The referring clinician suspected melanoma. Dermoscopy of a skin lesion. A female subject age 50: 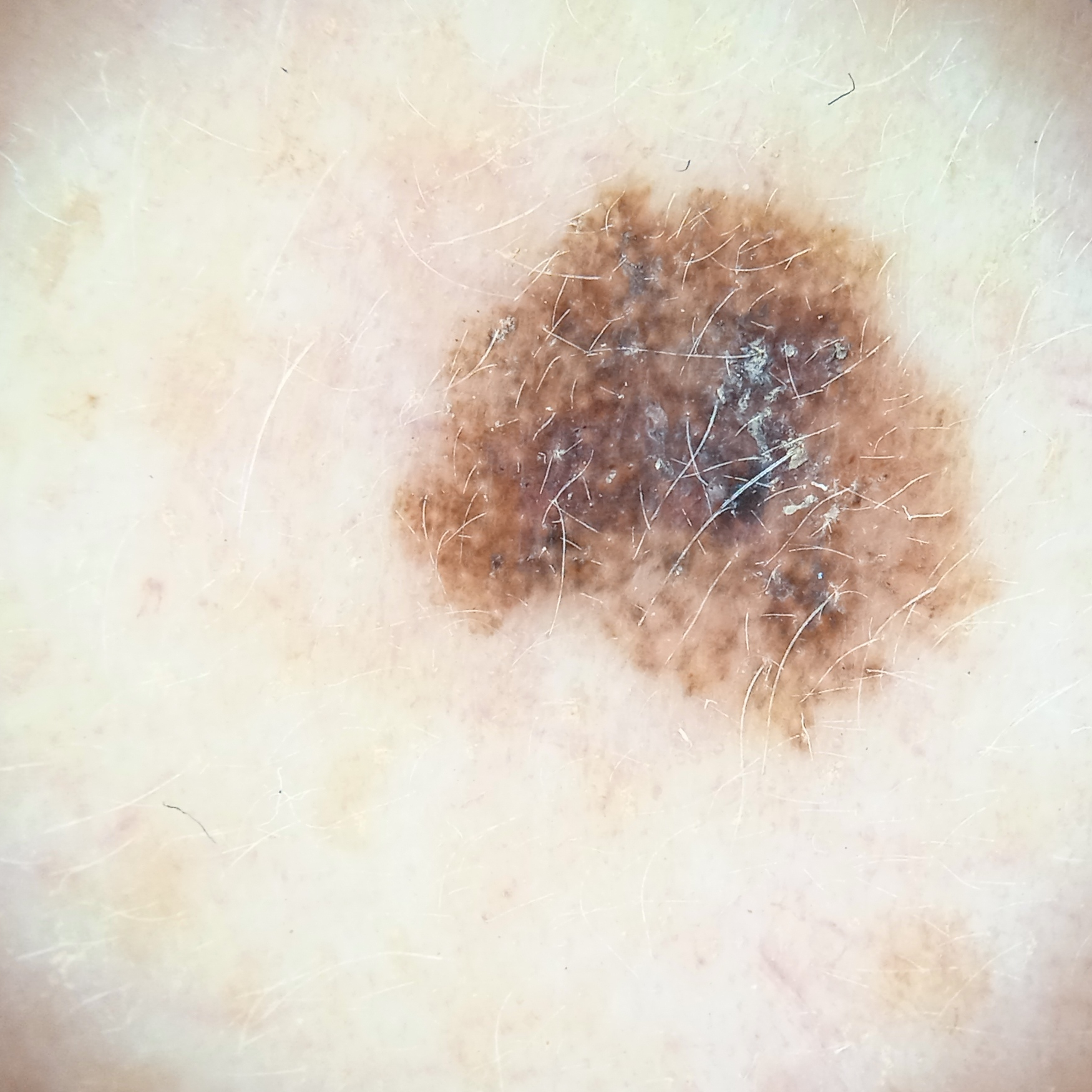site=the face
size=7 mm
pathology=melanoma (biopsy-proven)